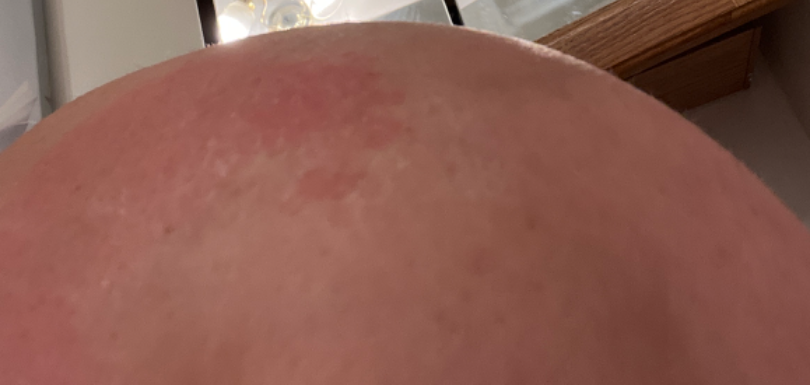The condition could not be reliably identified from the image. An image taken at an angle. The affected area is the arm.